An image taken at an angle; the affected area is the back of the torso, arm, front of the torso, back of the hand and leg:
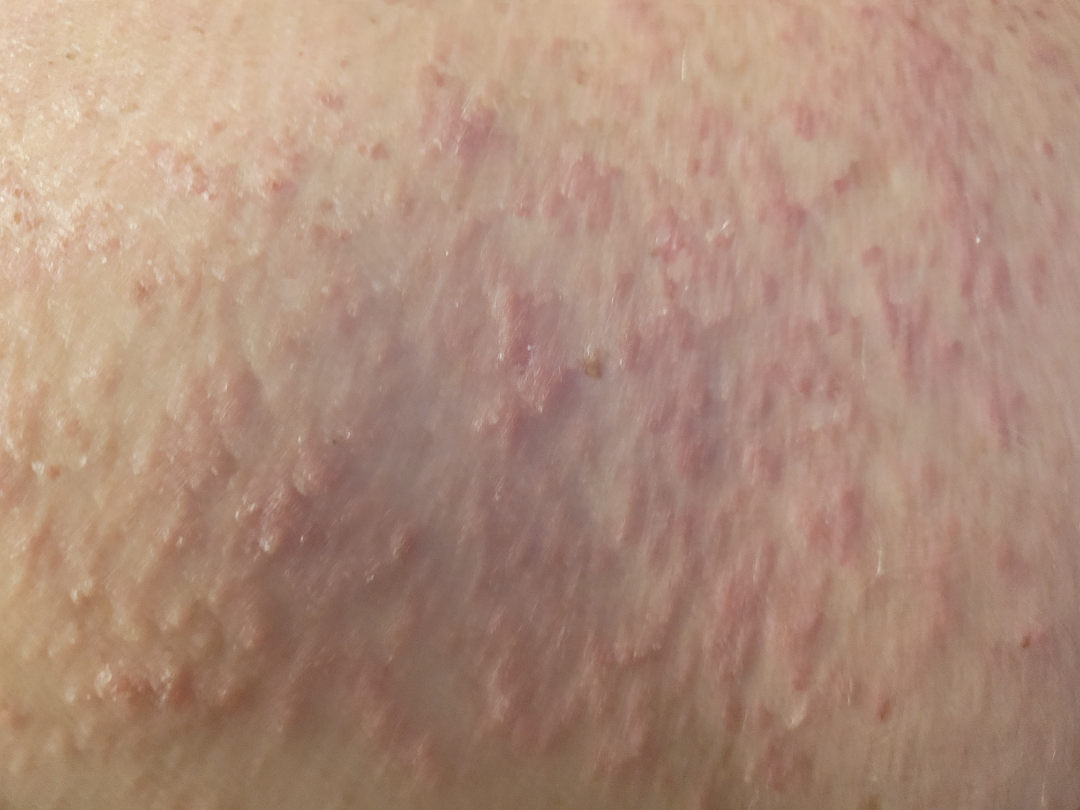The condition has been present for less than one week. Self-categorized by the patient as a rash. Fitzpatrick skin type II. Texture is reported as raised or bumpy. The lesion is associated with bothersome appearance and itching. The reviewing dermatologist's impression was: favoring Eczema; possibly Scabies; also on the differential is Allergic Contact Dermatitis.